Dermoscopy of a skin lesion.
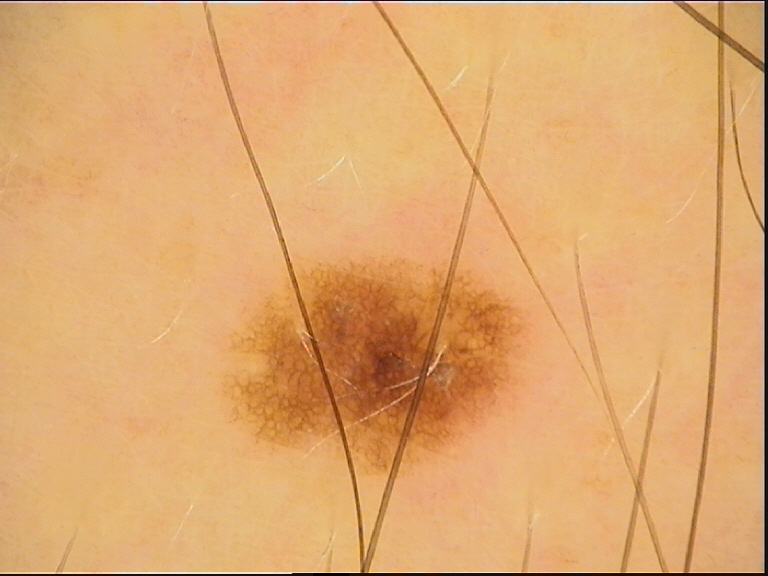label=junctional nevus (expert consensus).